The affected area is the arm · an image taken at an angle.
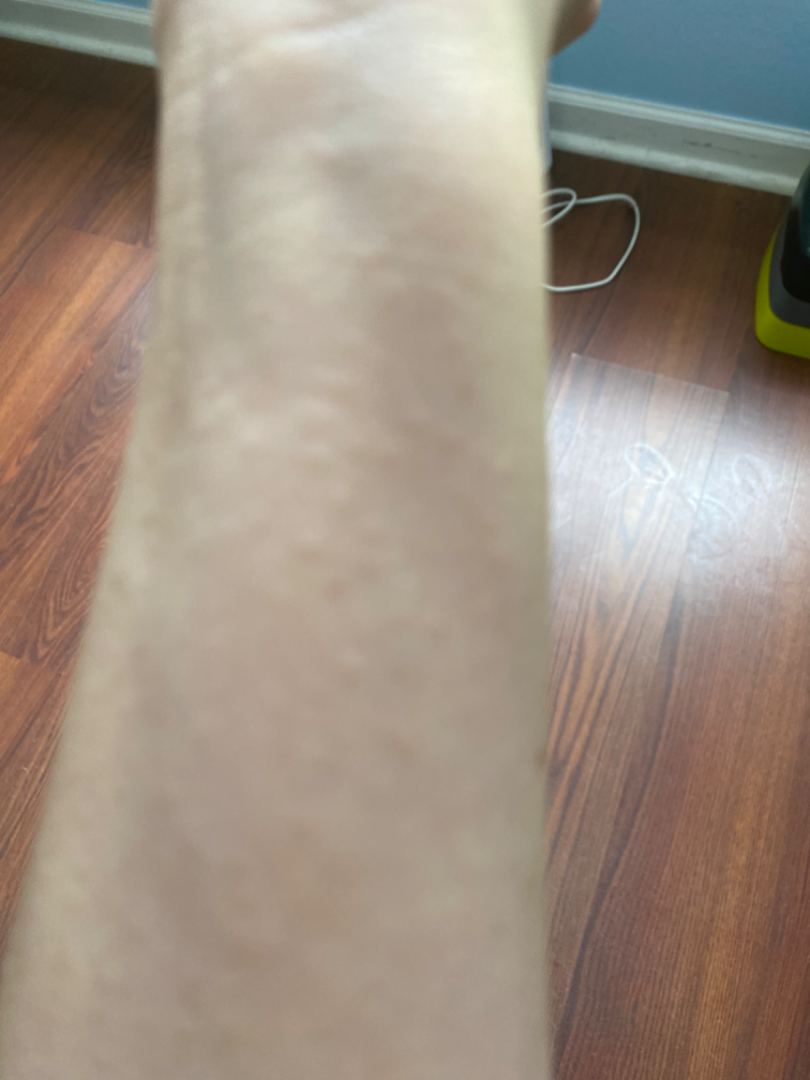<report>
<assessment>not assessable</assessment>
</report>